The lesion is described as flat; the subject is a female aged 40–49; the affected area is the top or side of the foot; the patient indicates the condition has been present for three to twelve months; the photograph was taken at an angle; the lesion is associated with bothersome appearance; the patient reported no systemic symptoms; the patient described the issue as a rash — 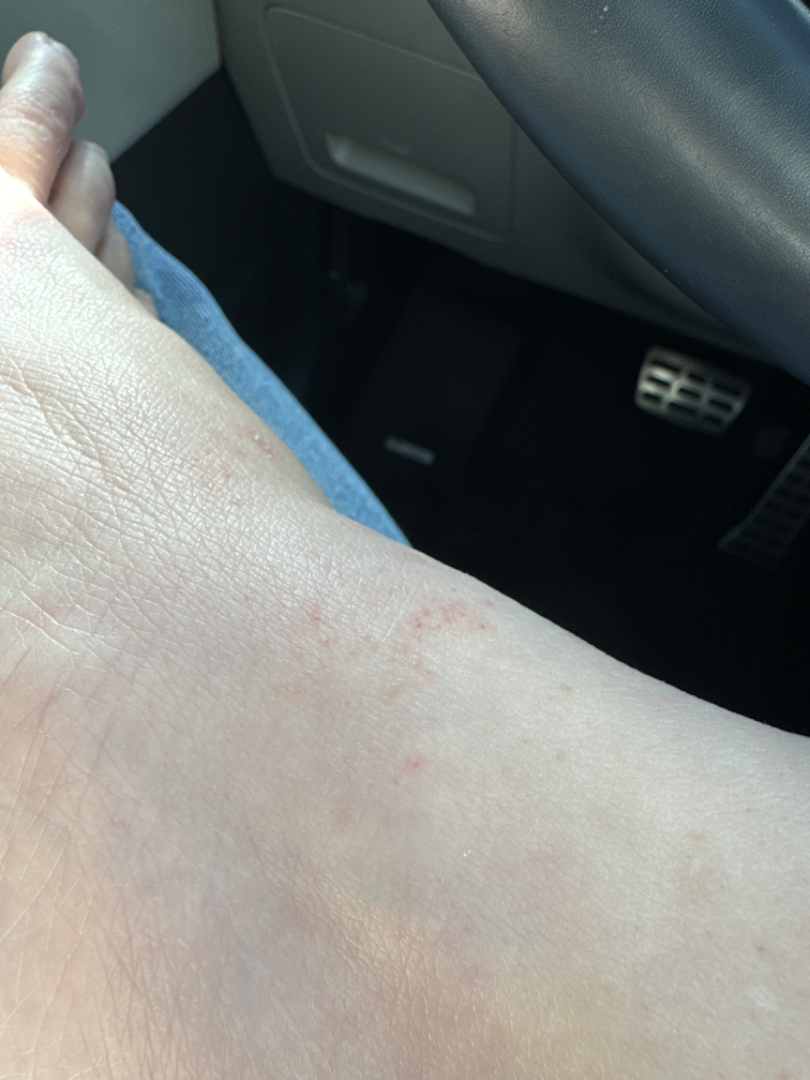On dermatologist assessment of the image: Pigmented purpuric eruption (weight 0.50); Eczema (weight 0.50).